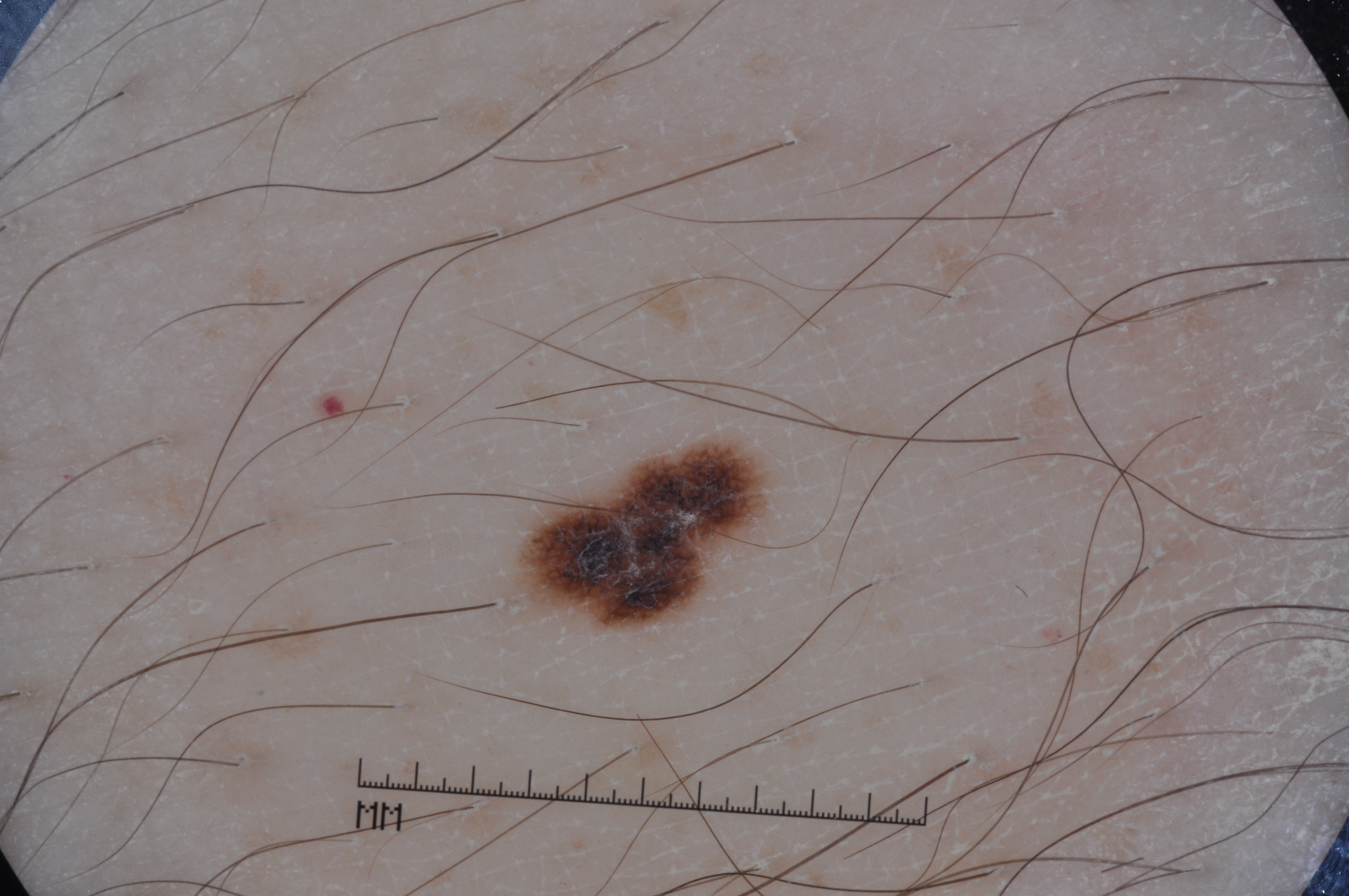imaging = dermoscopy of a skin lesion
subject = male, approximately 40 years of age
size = small
features = pigment network
location = (527, 449, 759, 623)
diagnosis = a melanocytic nevus, a benign lesion